The photograph was taken at an angle · female subject, age 18–29 · the head or neck and leg are involved: 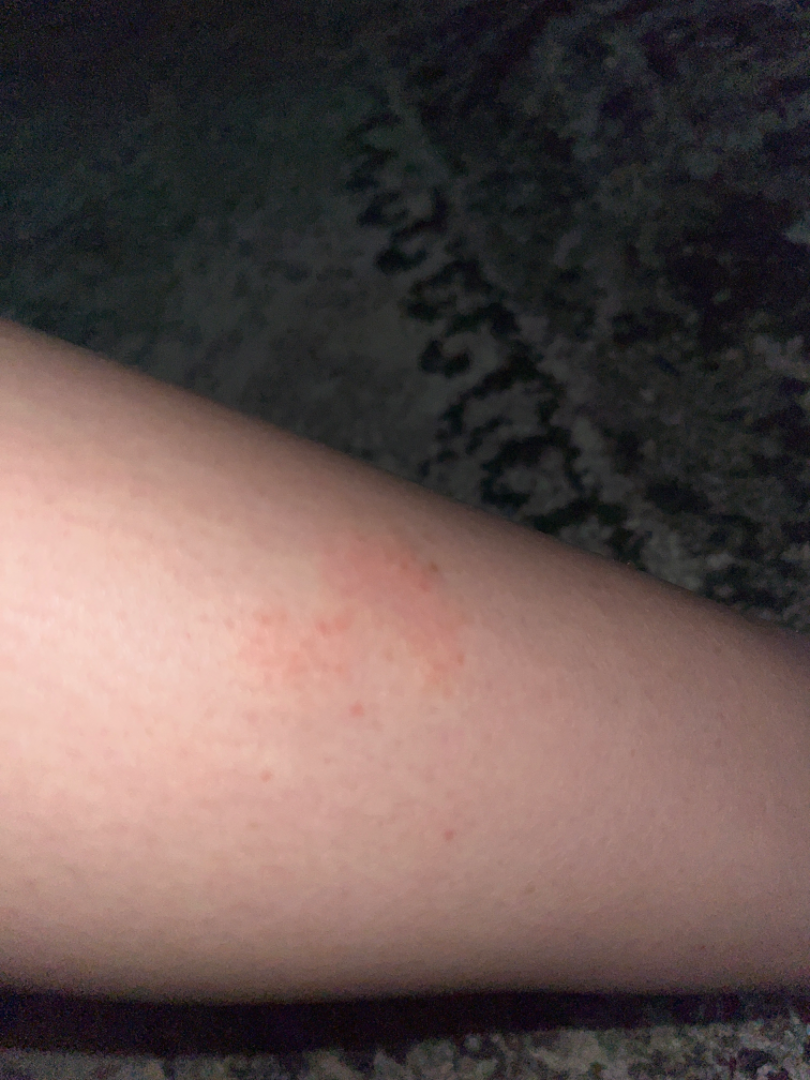{"patient_category": "a rash", "systemic_symptoms": ["joint pain", "fatigue"], "texture": ["rough or flaky", "raised or bumpy"], "symptoms": ["bothersome appearance", "burning", "itching", "pain"], "duration": "one to four weeks", "differential": {"tied_lead": ["Xerosis", "Eczema", "Irritant Contact Dermatitis"]}}